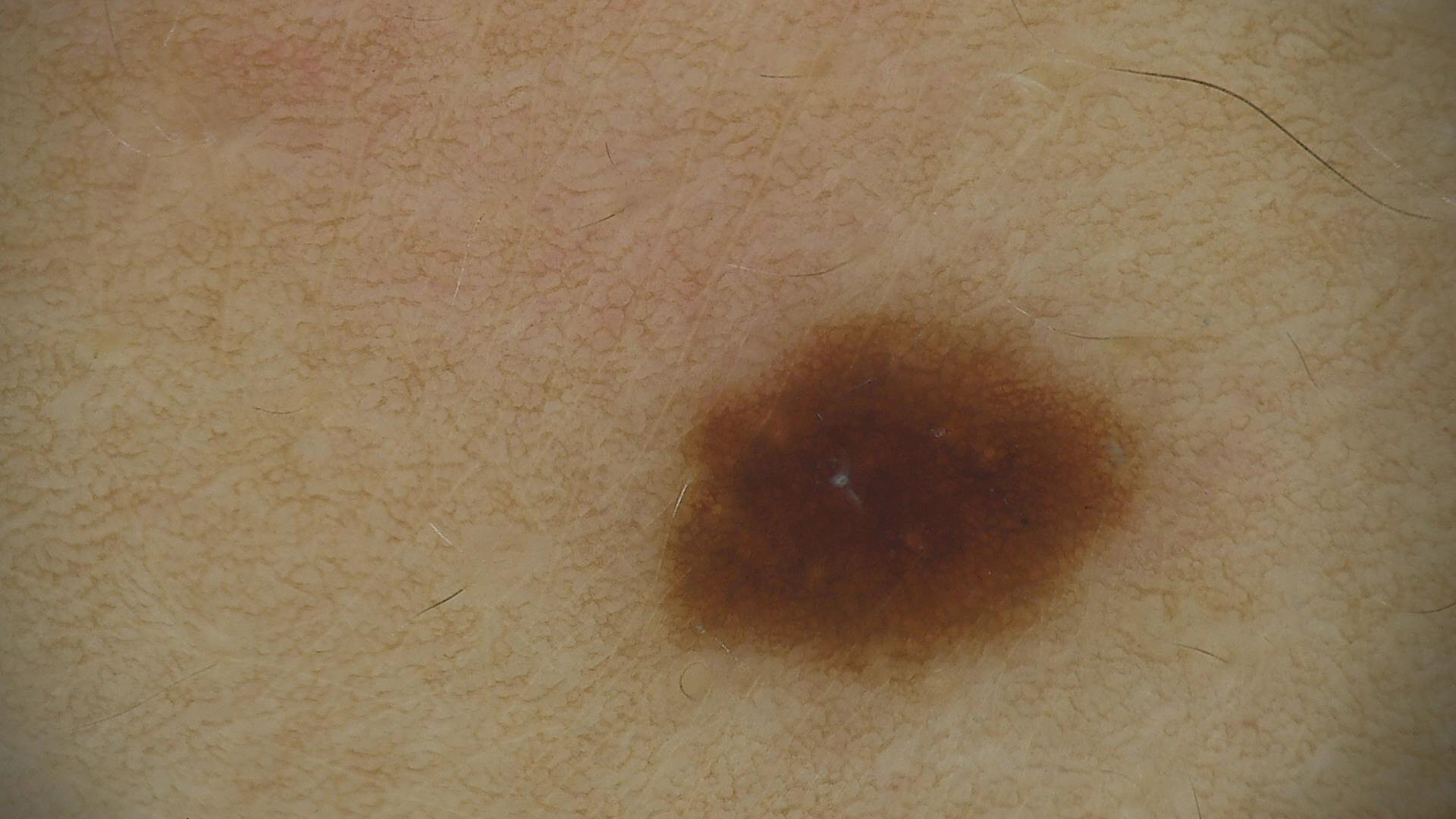A dermoscopic photograph of a skin lesion.
Labeled as a dysplastic junctional nevus.